Dermoscopy of a skin lesion · a male patient, about 75 years old — 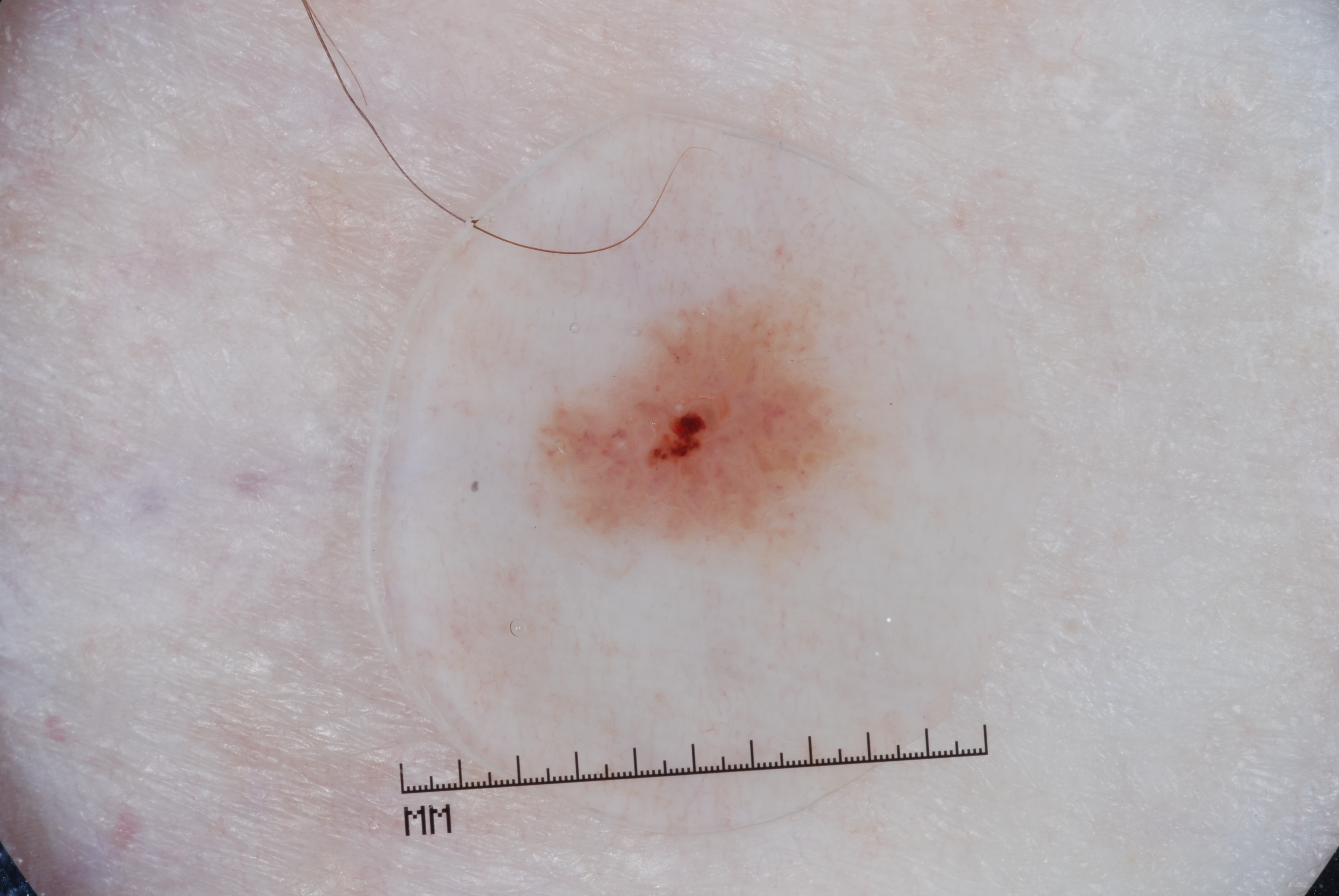lesion bbox = 534 281 868 553
dermoscopic features = milia-like cysts; absent: negative network, pigment network, and streaks
lesion size = ~6% of the field
diagnosis = a seborrheic keratosis